Female patient, age 50–59; the lesion is described as raised or bumpy; the affected area is the front of the torso; the photo was captured at a distance; the patient reported no relevant symptoms from the lesion: 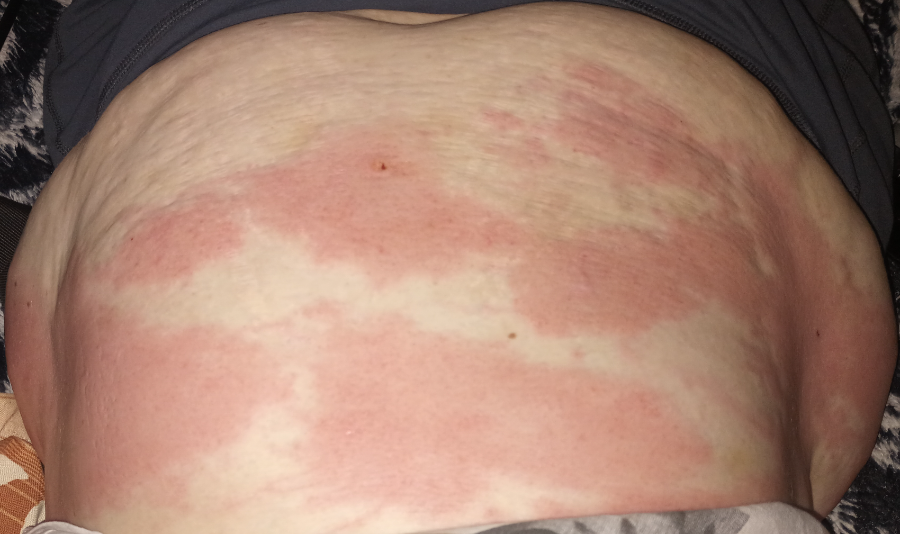Q: What is the differential diagnosis?
A: the differential includes Contact dermatitis and Urticaria, with no clear leading consideration